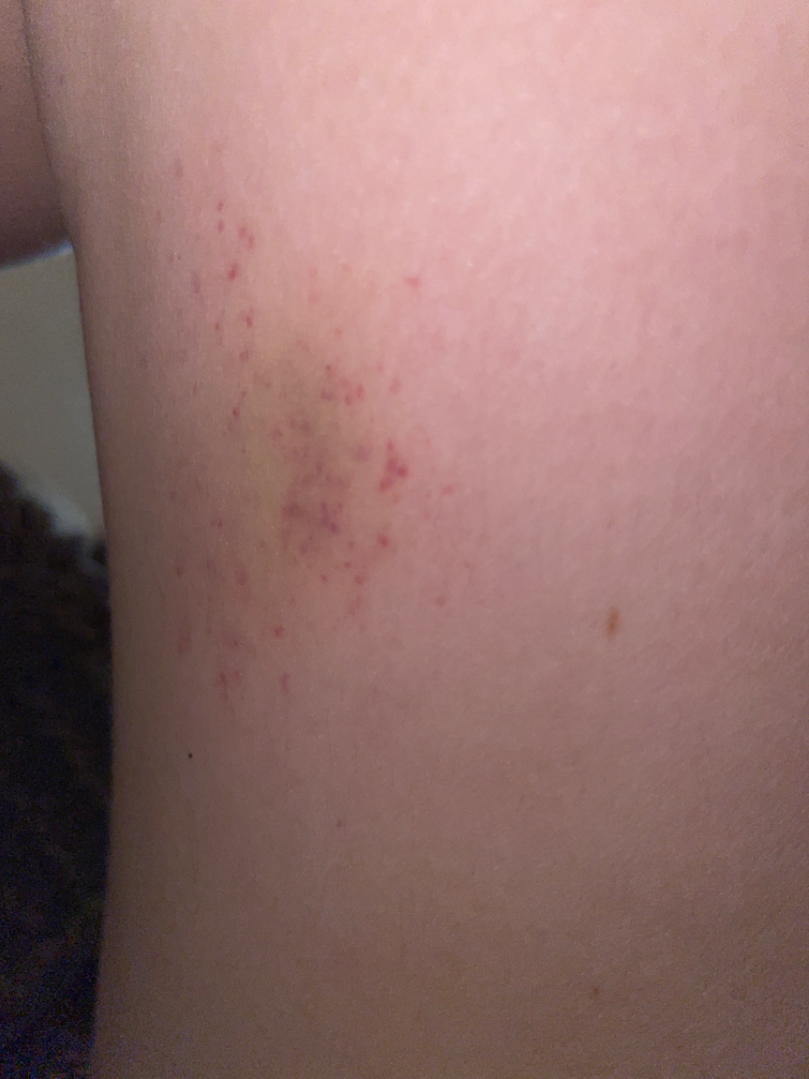Background: The leg is involved. The patient considered this a rash. This image was taken at an angle. The lesion is described as raised or bumpy. Skin tone: Fitzpatrick phototype III; human graders estimated a Monk skin tone scale of 2. Reported duration is about one day. No relevant lesion symptoms reported.